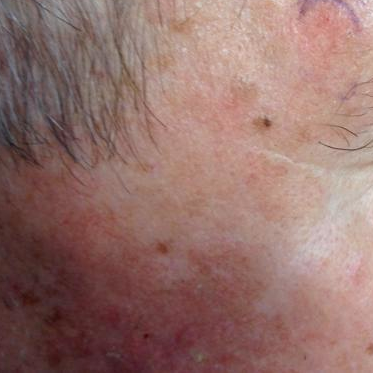<lesion>
<patient>
<age>52</age>
</patient>
<image>clinical photograph</image>
<lesion_location>the face</lesion_location>
<symptoms>none reported</symptoms>
<diagnosis>
<name>actinic keratosis</name>
<code>ACK</code>
<malignancy>indeterminate</malignancy>
<confirmation>clinical consensus</confirmation>
</diagnosis>
</lesion>